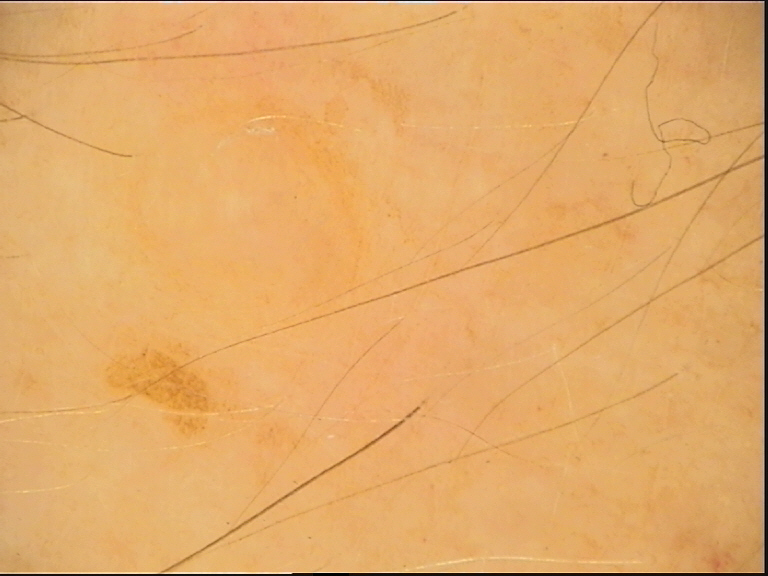<dermoscopy>
  <image>dermatoscopy</image>
  <lesion_type>
    <main_class>keratinocytic</main_class>
  </lesion_type>
  <diagnosis>
    <name>seborrheic keratosis</name>
    <code>sk</code>
    <malignancy>benign</malignancy>
    <super_class>non-melanocytic</super_class>
    <confirmation>expert consensus</confirmation>
  </diagnosis>
</dermoscopy>